A close-up photograph:
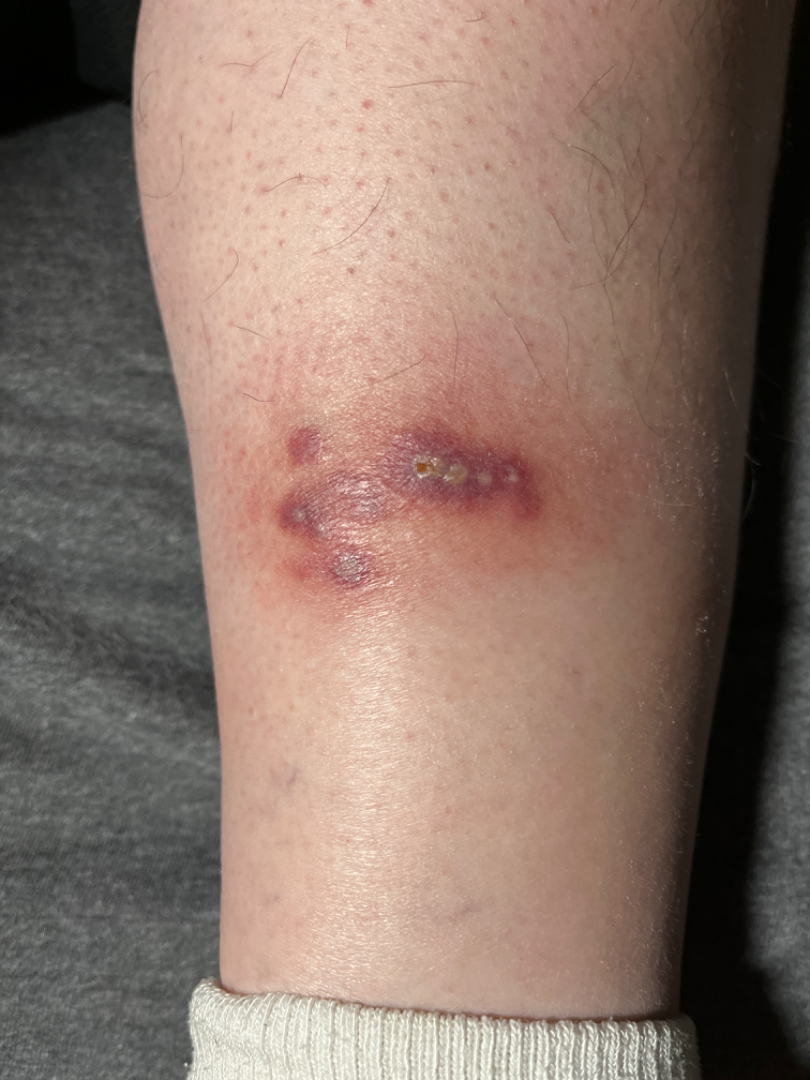On photographic review by a dermatologist: the impression was split between Insect Bite and Pyoderma Gangrenosum.